A dermoscopic photograph of a skin lesion: 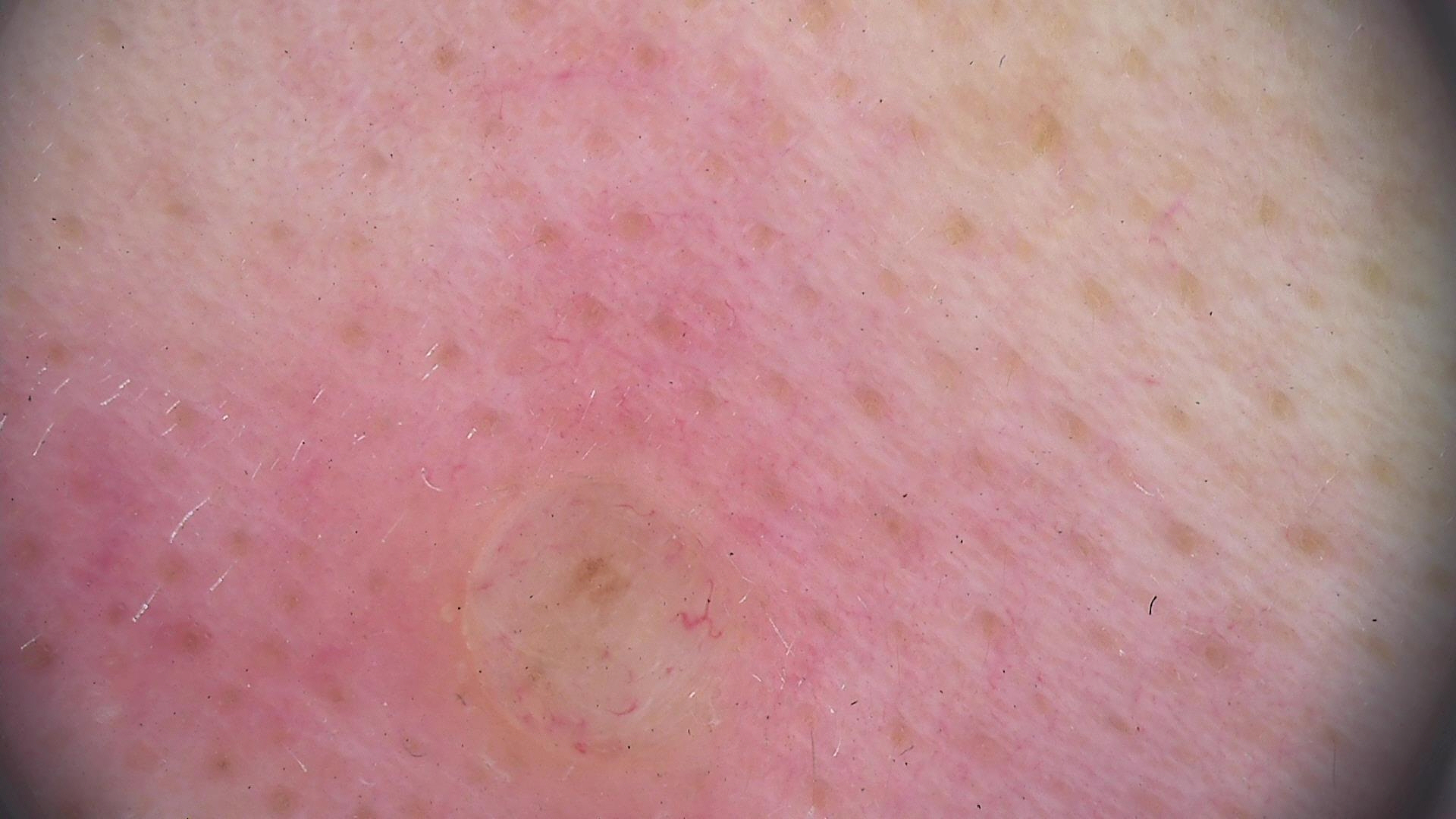Classified as a banal lesion — a dermal nevus.